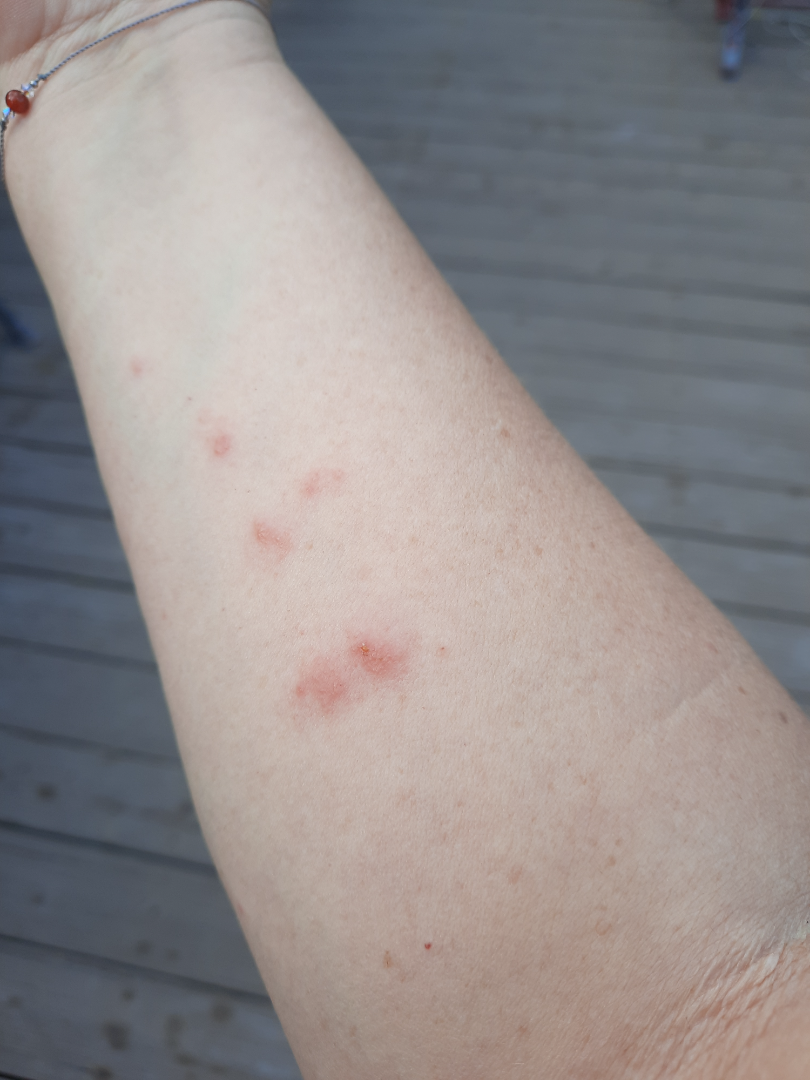| key | value |
|---|---|
| patient describes the issue as | a rash |
| constitutional symptoms | fatigue |
| skin tone | human graders estimated MST 3 or 4 (two reviewer pools) |
| anatomic site | leg, arm and front of the torso |
| photo taken | at an angle |
| lesion texture | raised or bumpy |
| symptoms | itching |
| differential | Psoriasis, Eczema and Allergic Contact Dermatitis were considered with similar weight |